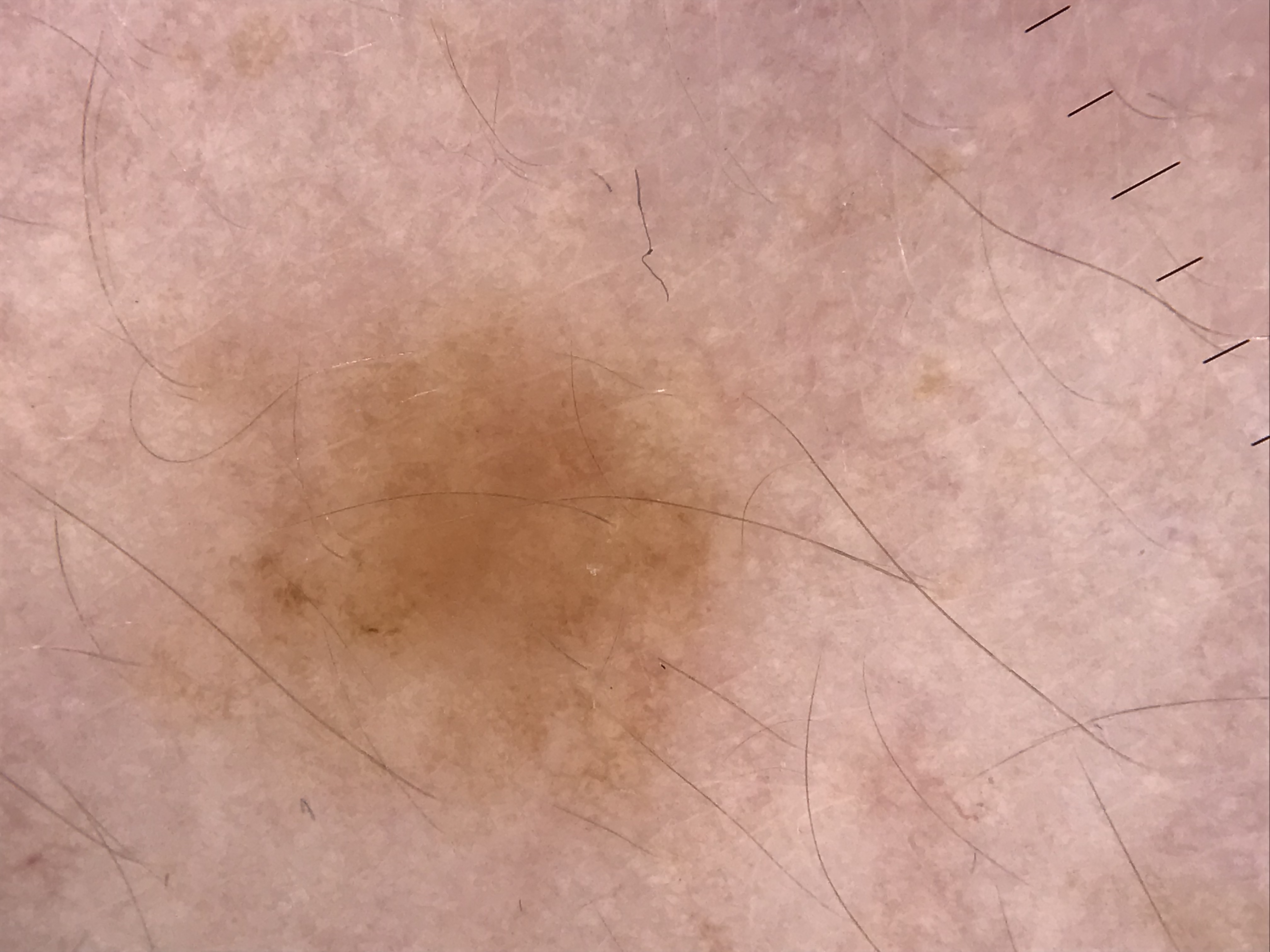assessment=dysplastic junctional nevus (expert consensus).